The leg is involved; female contributor, age 60–69; close-up view — 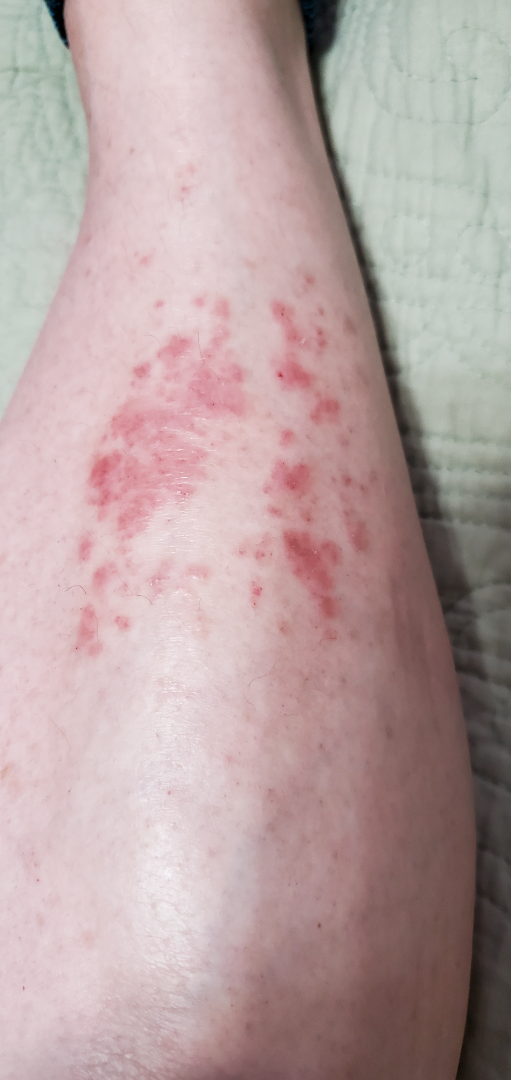Review: Most consistent with Allergic Contact Dermatitis; possibly Eczema; with consideration of Pigmented purpuric eruption.